The lesion involves the arm · an image taken at an angle:
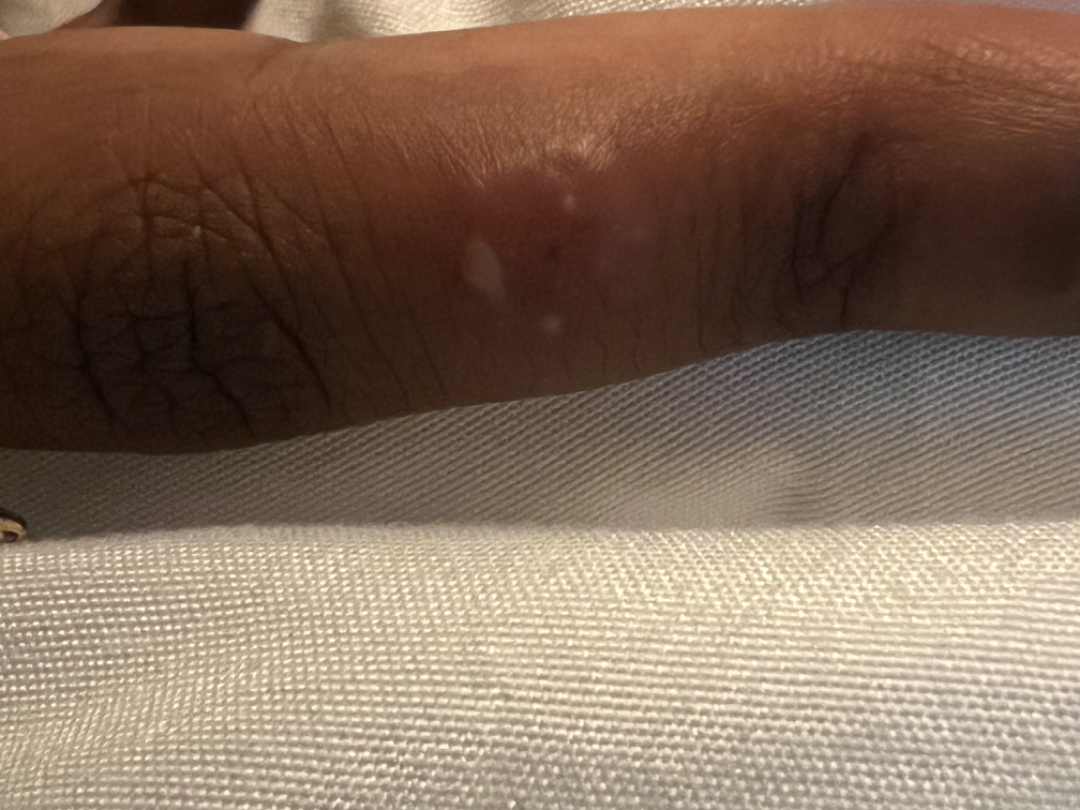Findings:
The skin findings could not be characterized from the image.
Background:
Texture is reported as raised or bumpy. The patient reports the condition has been present for about one day.